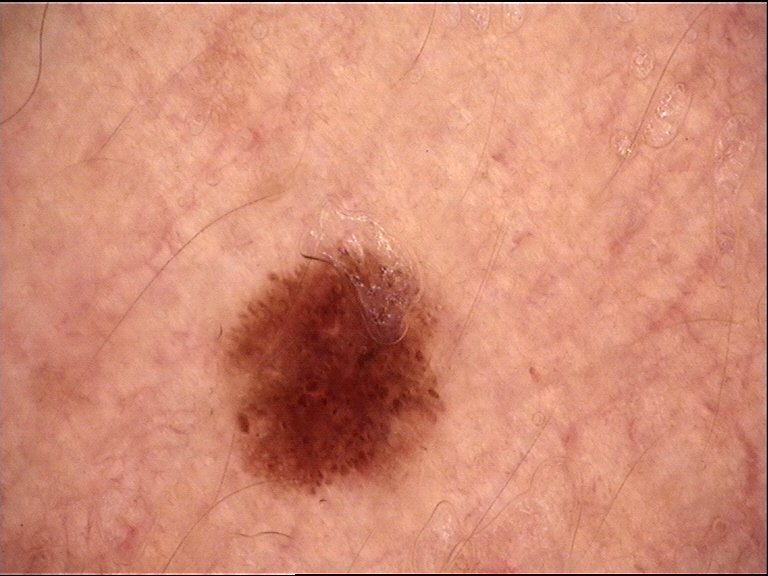• image type · dermatoscopy
• diagnosis · dysplastic junctional nevus (expert consensus)